A dermoscopic view of a skin lesion. A male patient, aged approximately 65:
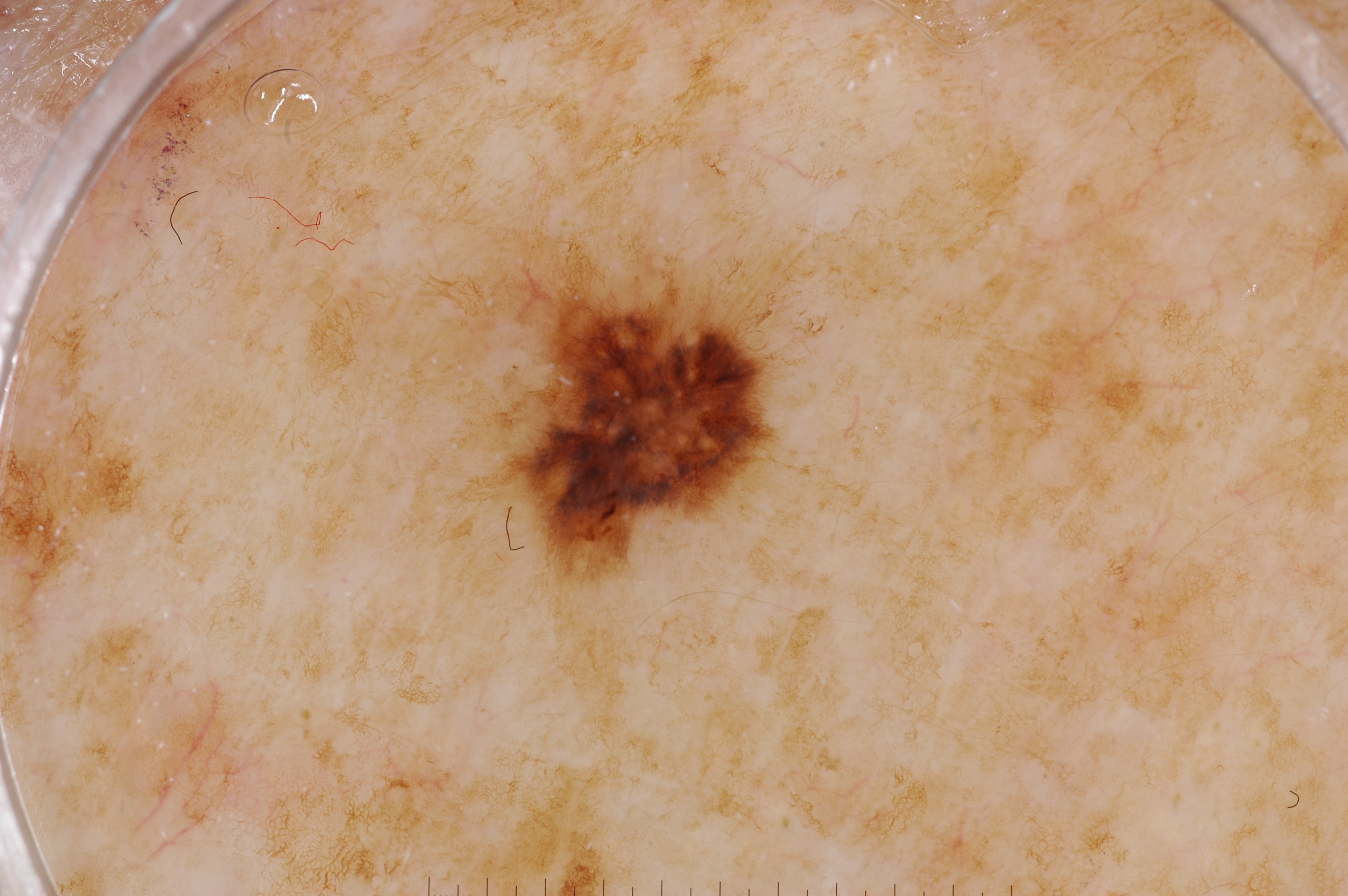The lesion covers approximately 5% of the dermoscopic field. As (left, top, right, bottom), the lesion is bounded by <box>499, 273, 785, 593</box>. Dermoscopic examination shows milia-like cysts and pigment network, with no negative network or streaks. The biopsy diagnosis was a melanoma.